A dermatoscopic image of a skin lesion.
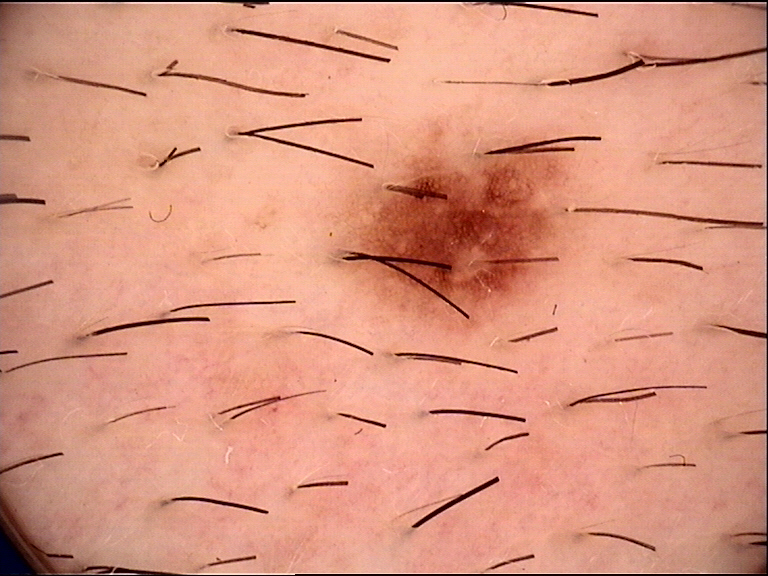label=dysplastic junctional nevus (expert consensus).